A clinical close-up photograph of a skin lesion · a patient 79 years old — 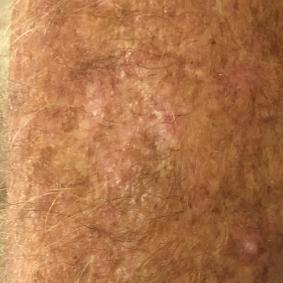The lesion was found on a forearm. By the patient's account, the lesion itches, but has not grown and does not hurt. Consistent with an actinic keratosis.